The lesion involves the arm; the photo was captured at a distance — 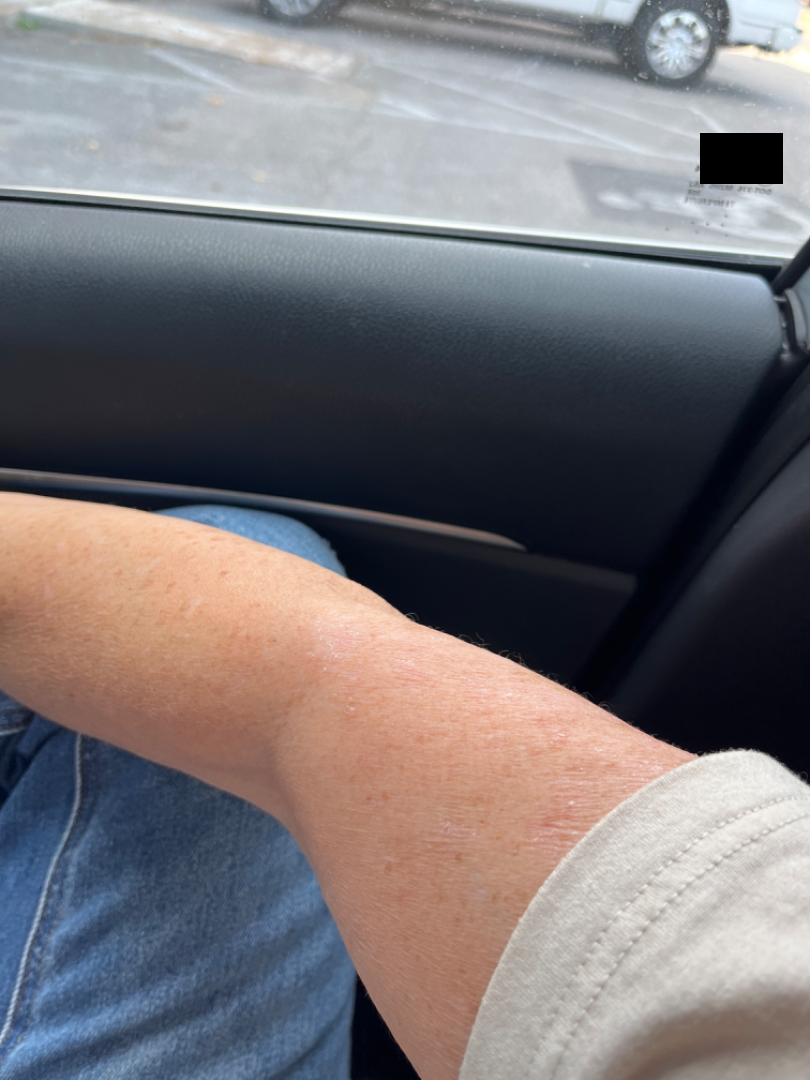diagnostic considerations: most consistent with Eczema.